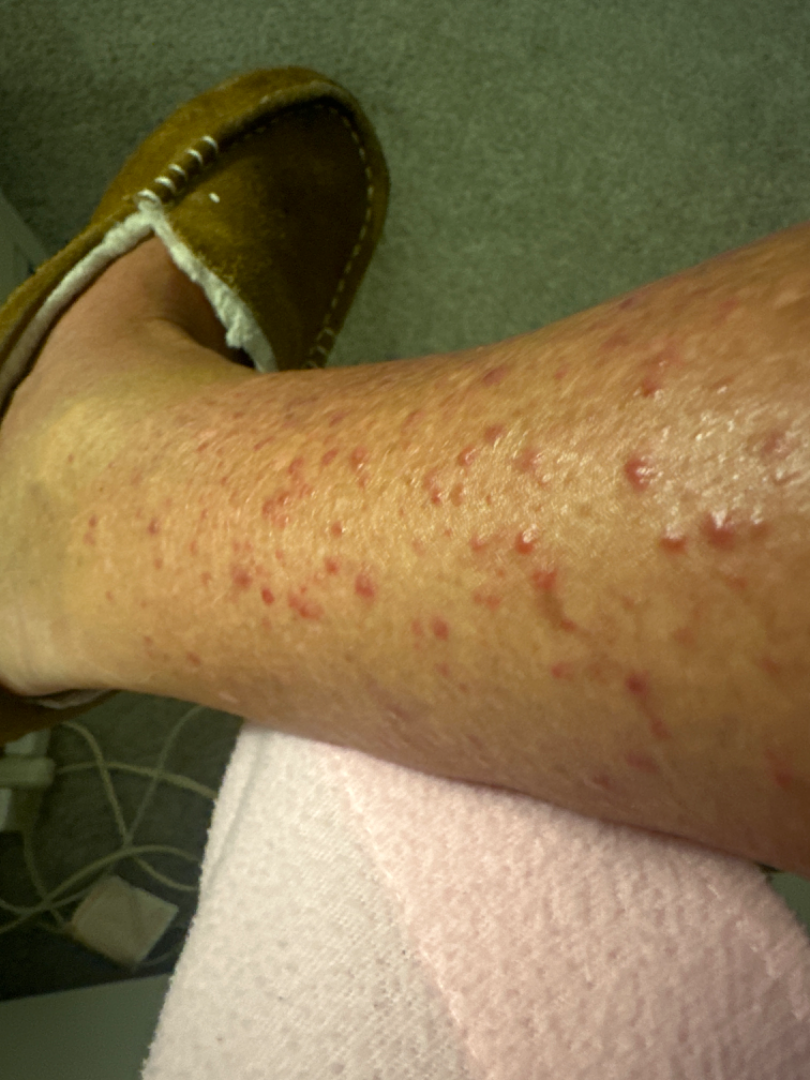present for: less than one week | surface texture: raised or bumpy | patient: female, age 50–59 | body site: leg and arm | photo taken: close-up | differential: the leading impression is Hypersensitivity; also consider Lichen planus/lichenoid eruption.